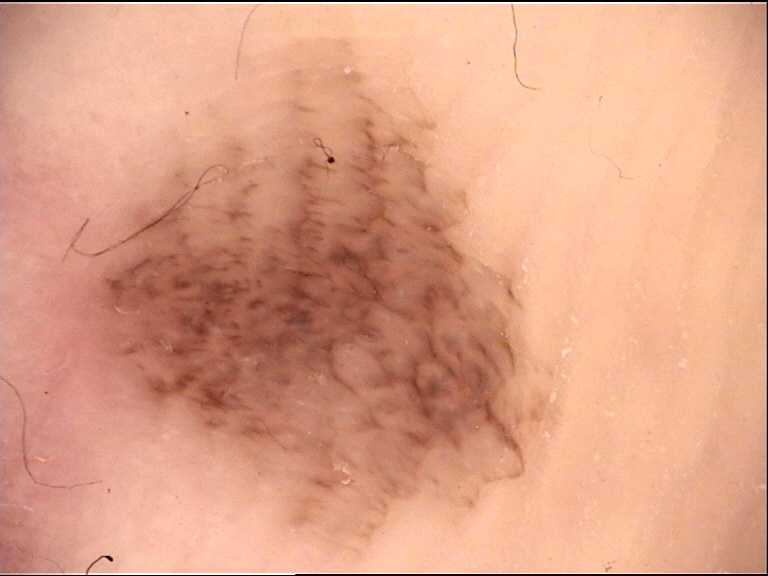Q: What kind of image is this?
A: dermatoscopy
Q: What was the diagnostic impression?
A: acral compound nevus (expert consensus)